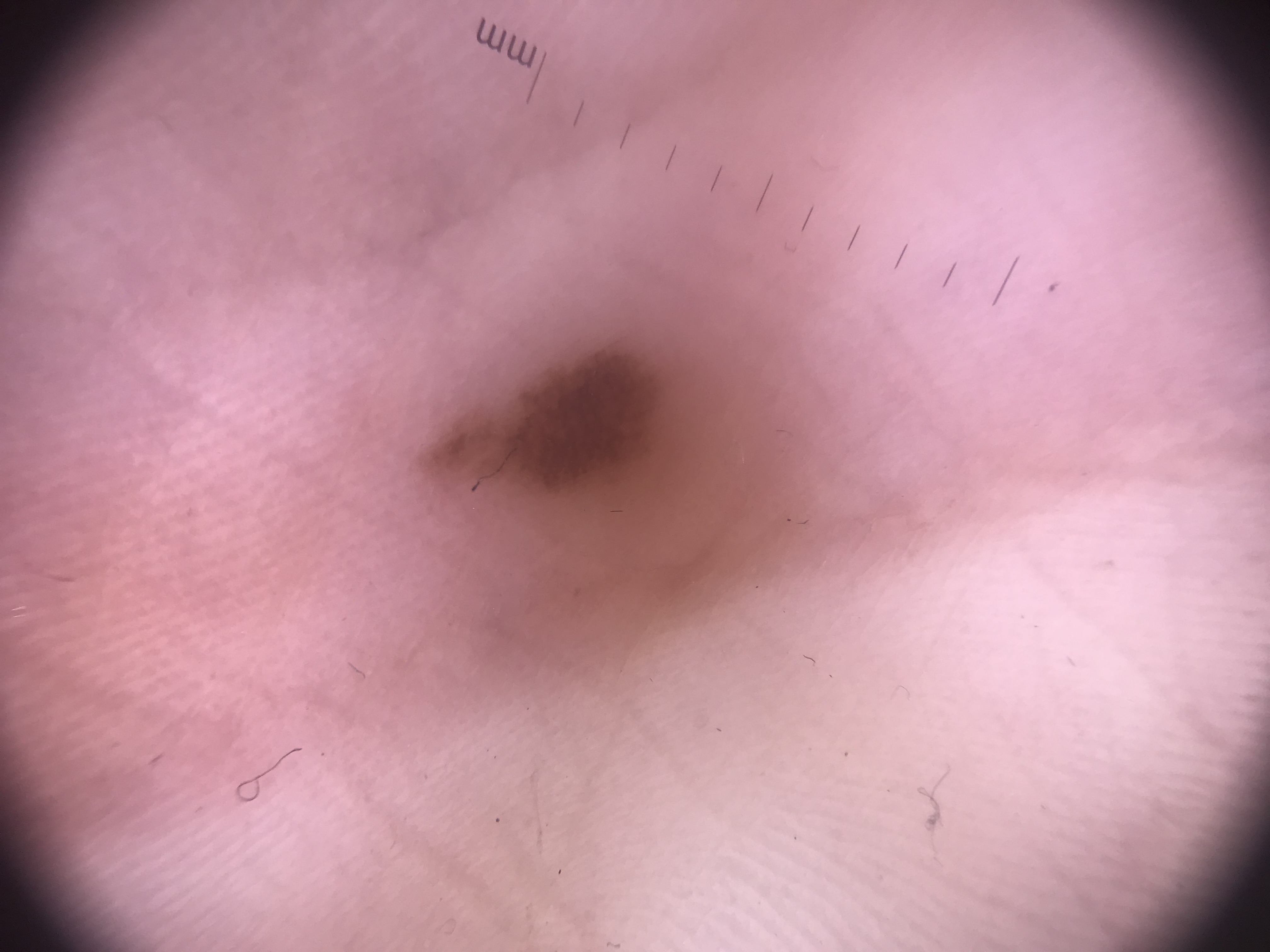The diagnostic label was an acral junctional nevus.